A dermoscopic photograph of a skin lesion.
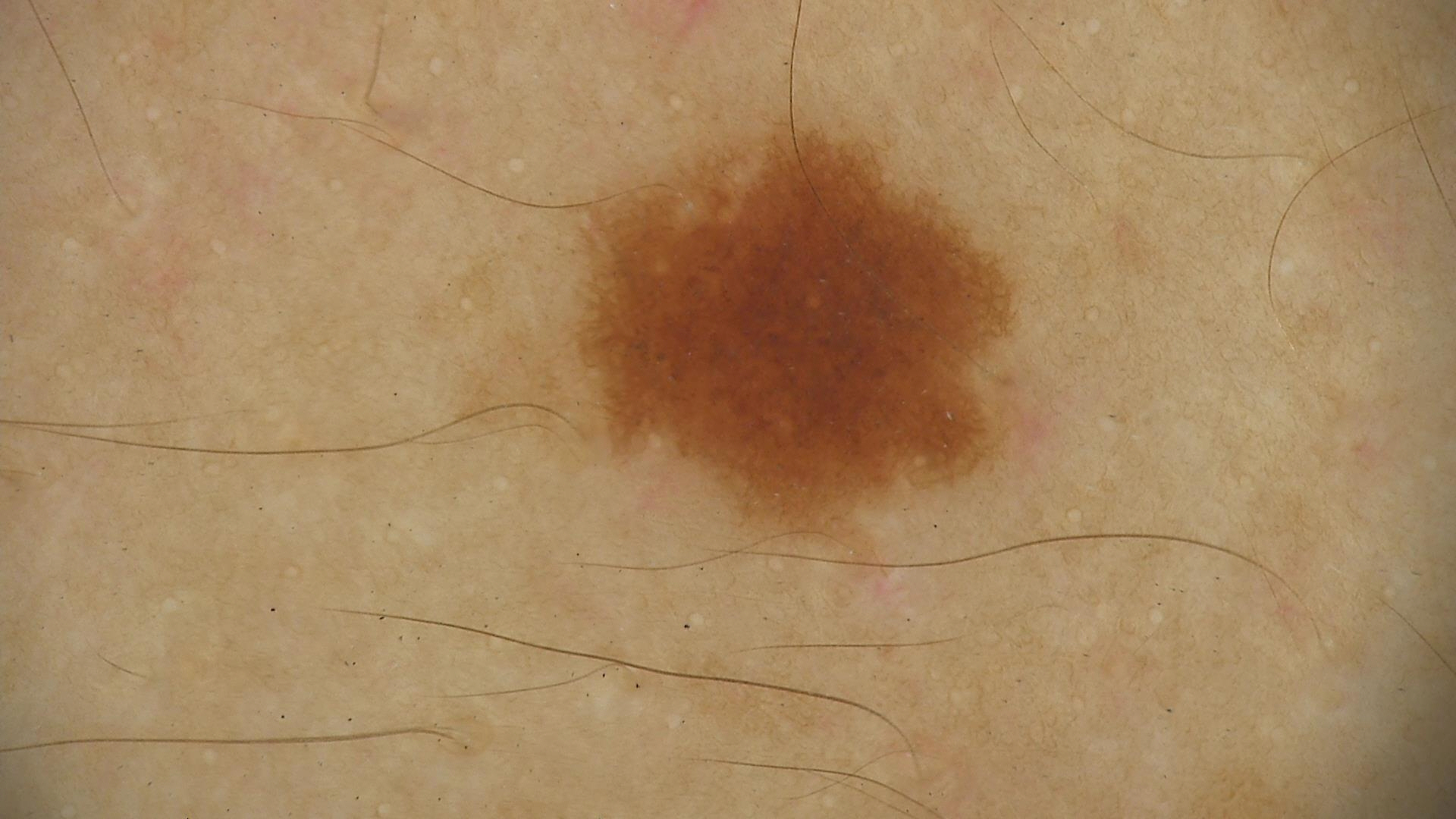  diagnosis:
    name: dysplastic junctional nevus
    code: jd
    malignancy: benign
    super_class: melanocytic
    confirmation: expert consensus